The lesion involves the head or neck, front of the torso and arm; the contributor is a female aged 40–49; the photo was captured at an angle — 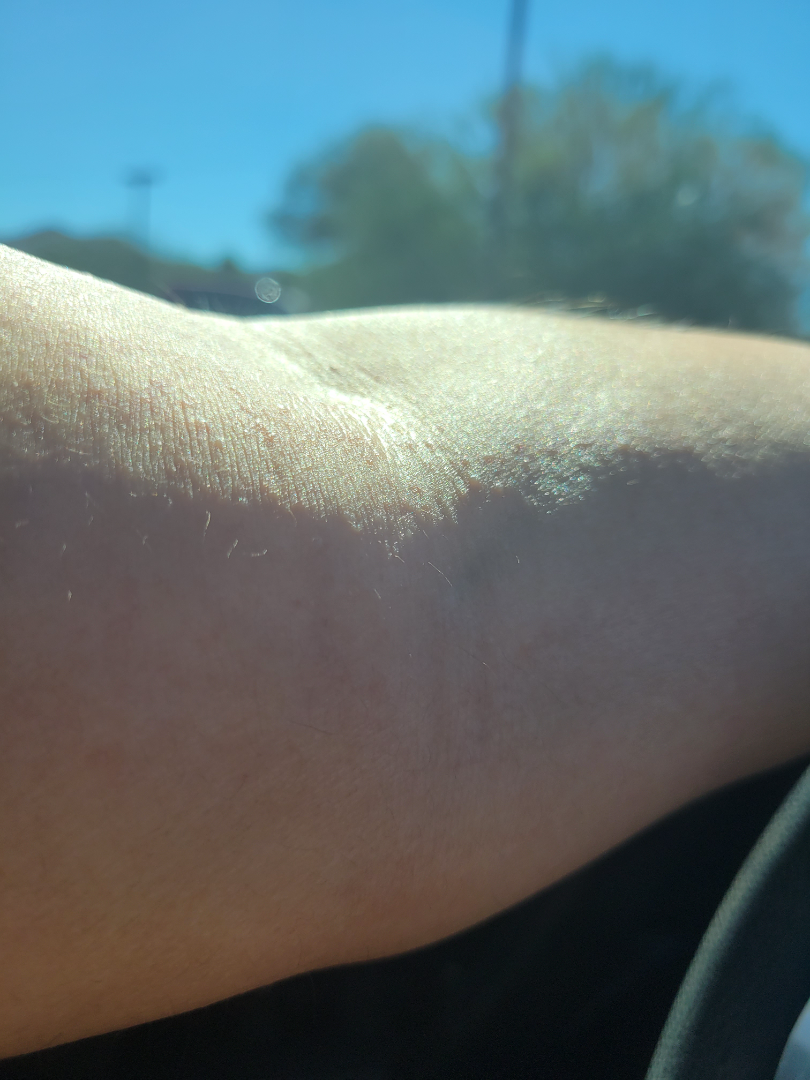Diagnostic features were not clearly distinguishable in this photograph. The patient reports the condition has been present for about one day. Self-categorized by the patient as a rash. Symptoms reported: itching and bothersome appearance. The patient reports the lesion is raised or bumpy. The patient reported no systemic symptoms.